A dermoscopy image of a single skin lesion.
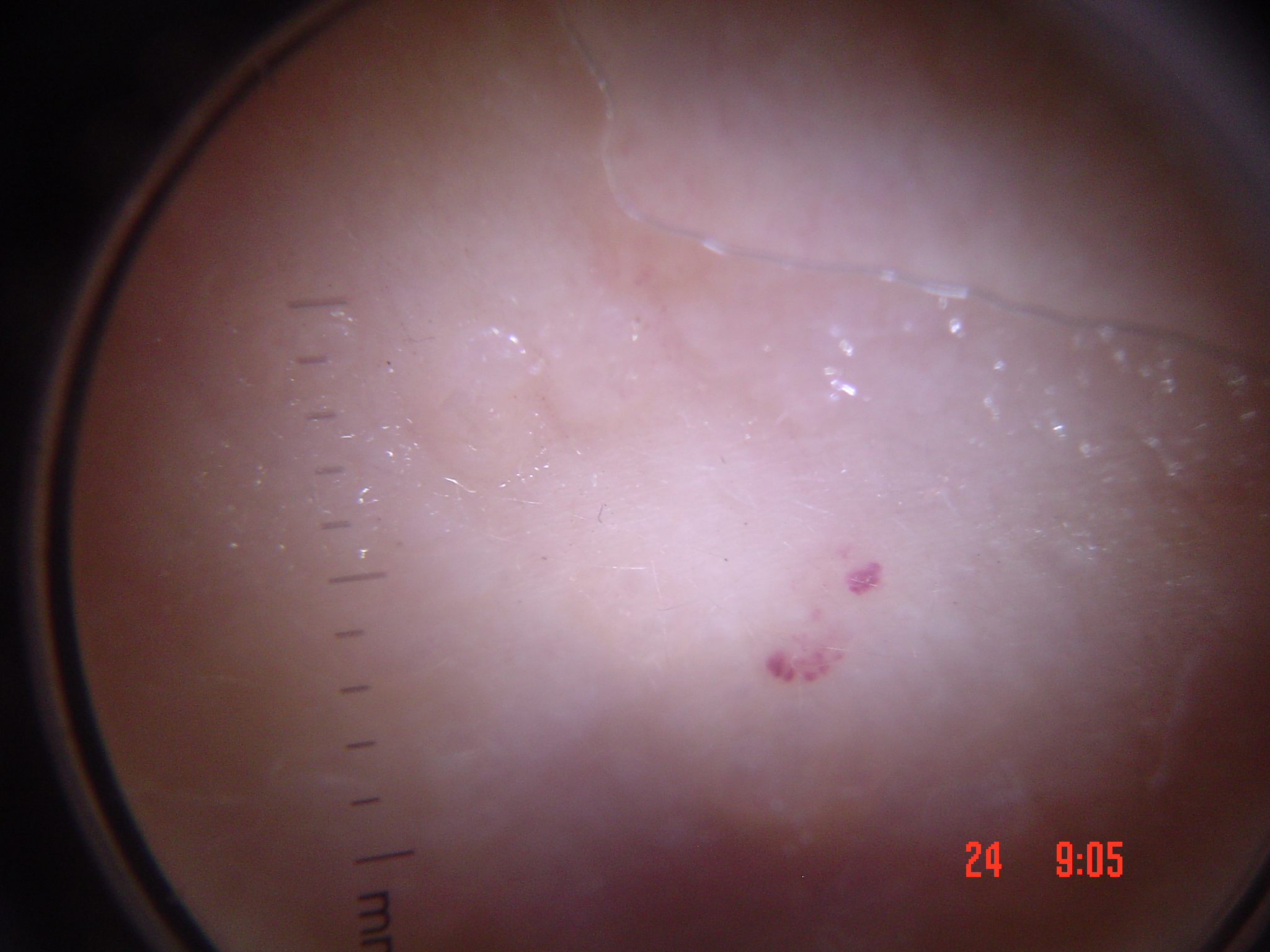Findings:
The morphology is that of a vascular lesion.
Impression:
Labeled as a hemangioma.